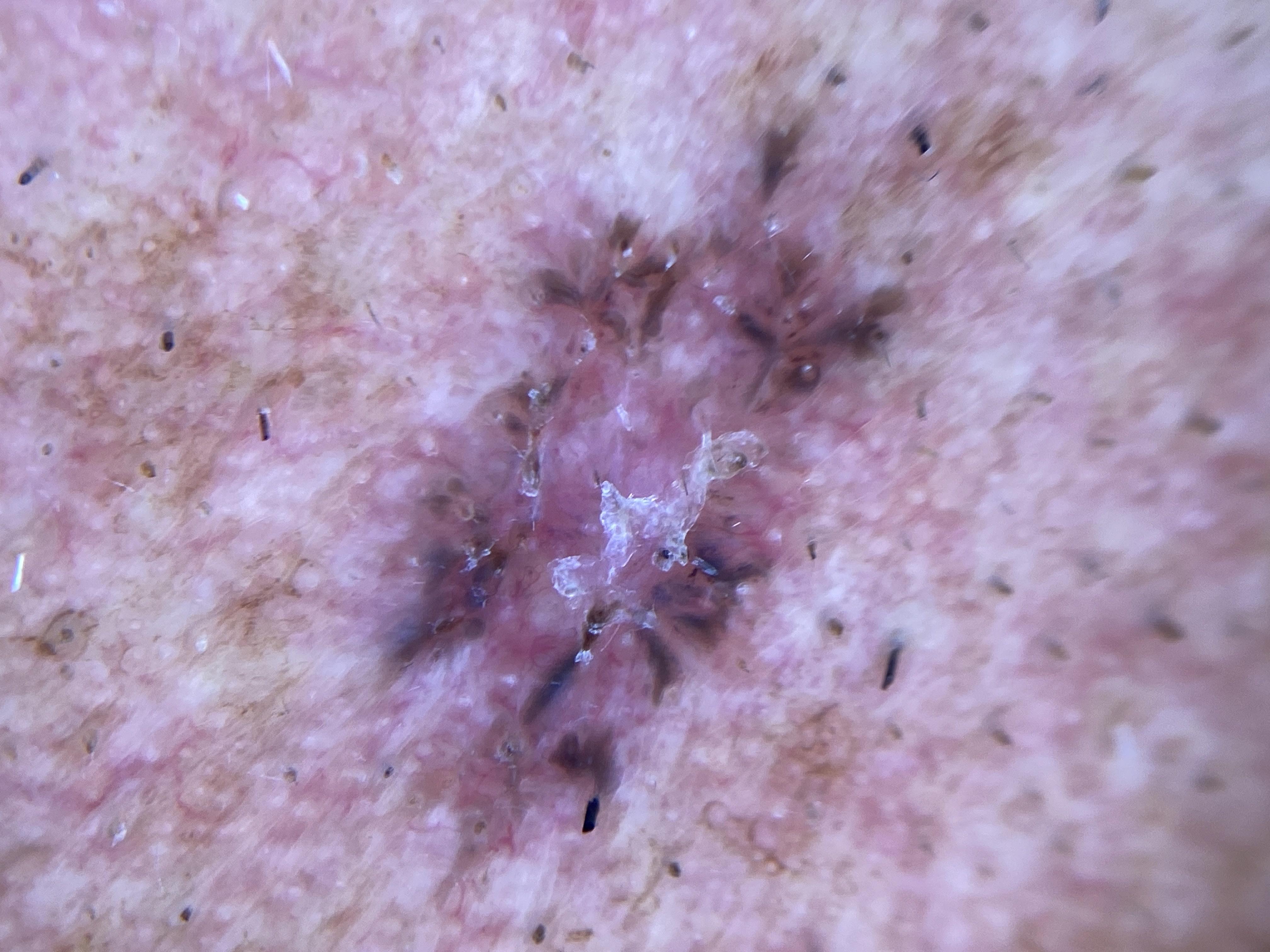Case:
* subject · male, in their mid- to late 80s or older
* anatomic site · the head or neck
* diagnosis · Basal cell carcinoma (biopsy-proven)